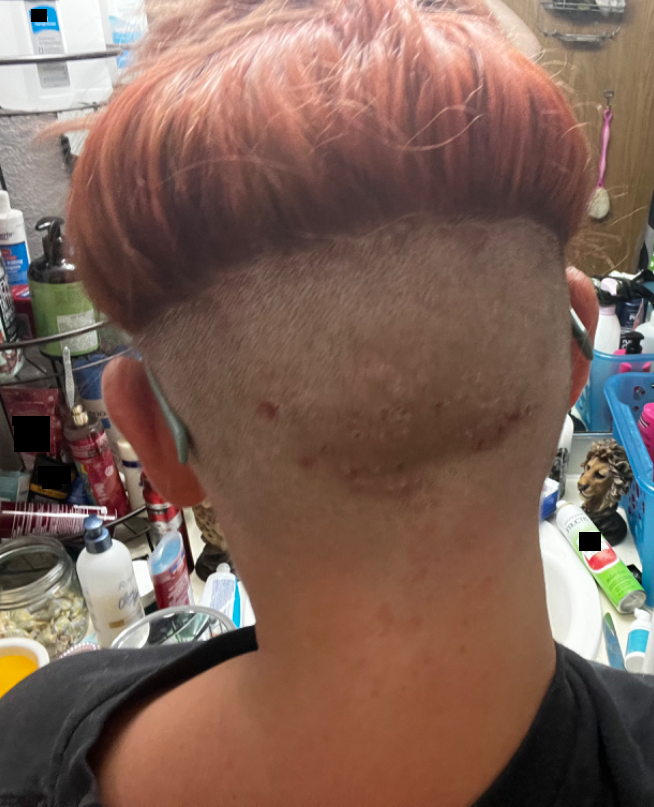No relevant systemic symptoms. The patient considered this a rash. Located on the head or neck. The subject is 18–29, female. The contributor notes the condition has been present for since childhood. The contributor notes enlargement, itching, burning, pain, bleeding and bothersome appearance. An image taken at a distance. A single dermatologist reviewed the case: the favored diagnosis is Acne keloidalis; possibly Folliculitis decalvans.